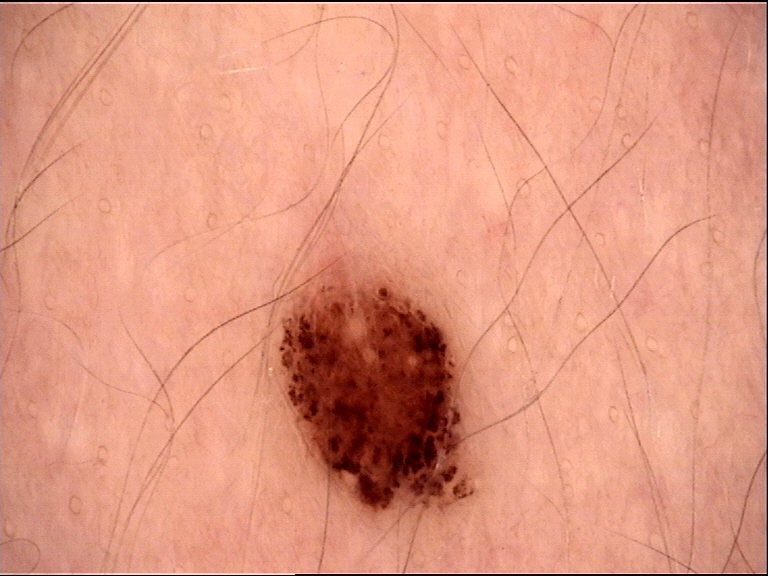A skin lesion imaged with a dermatoscope. The architecture is that of a banal lesion. The diagnostic label was a compound nevus.